The patient reported no systemic symptoms, the patient considered this a rash, the lesion is described as fluid-filled, the photo was captured at a distance, the condition has been present for less than one week, reported lesion symptoms include itching, the affected area is the arm and leg.
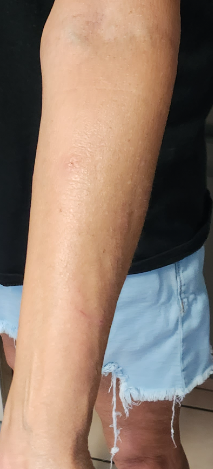Case summary:
- impression · most likely Animal bite - wound; also on the differential is Inflicted skin lesions; less probable is Eczema